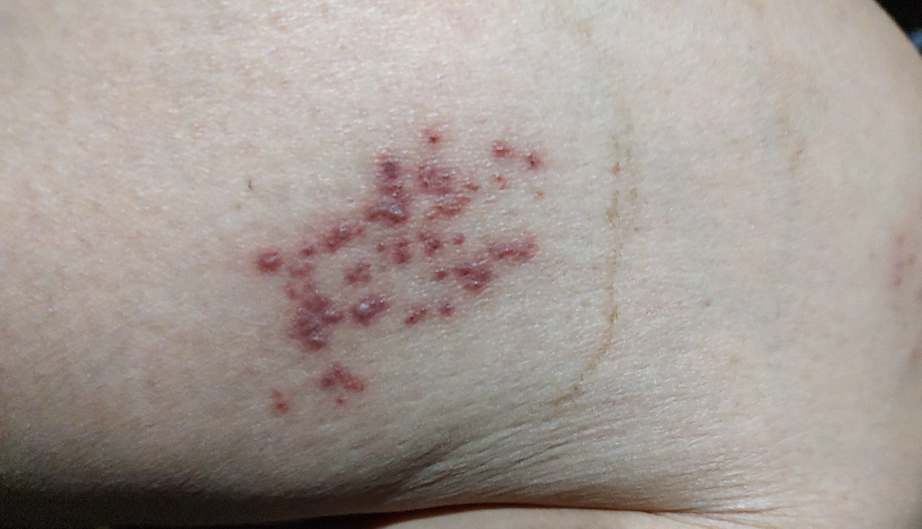Symptoms reported: bothersome appearance.
The patient notes the condition has been present for less than one week.
The subject is 50–59, female.
The leg is involved.
The photo was captured at an angle.
The patient notes the lesion is raised or bumpy and flat.
Self-categorized by the patient as a rash.
On remote review of the image: most likely Herpes Zoster.